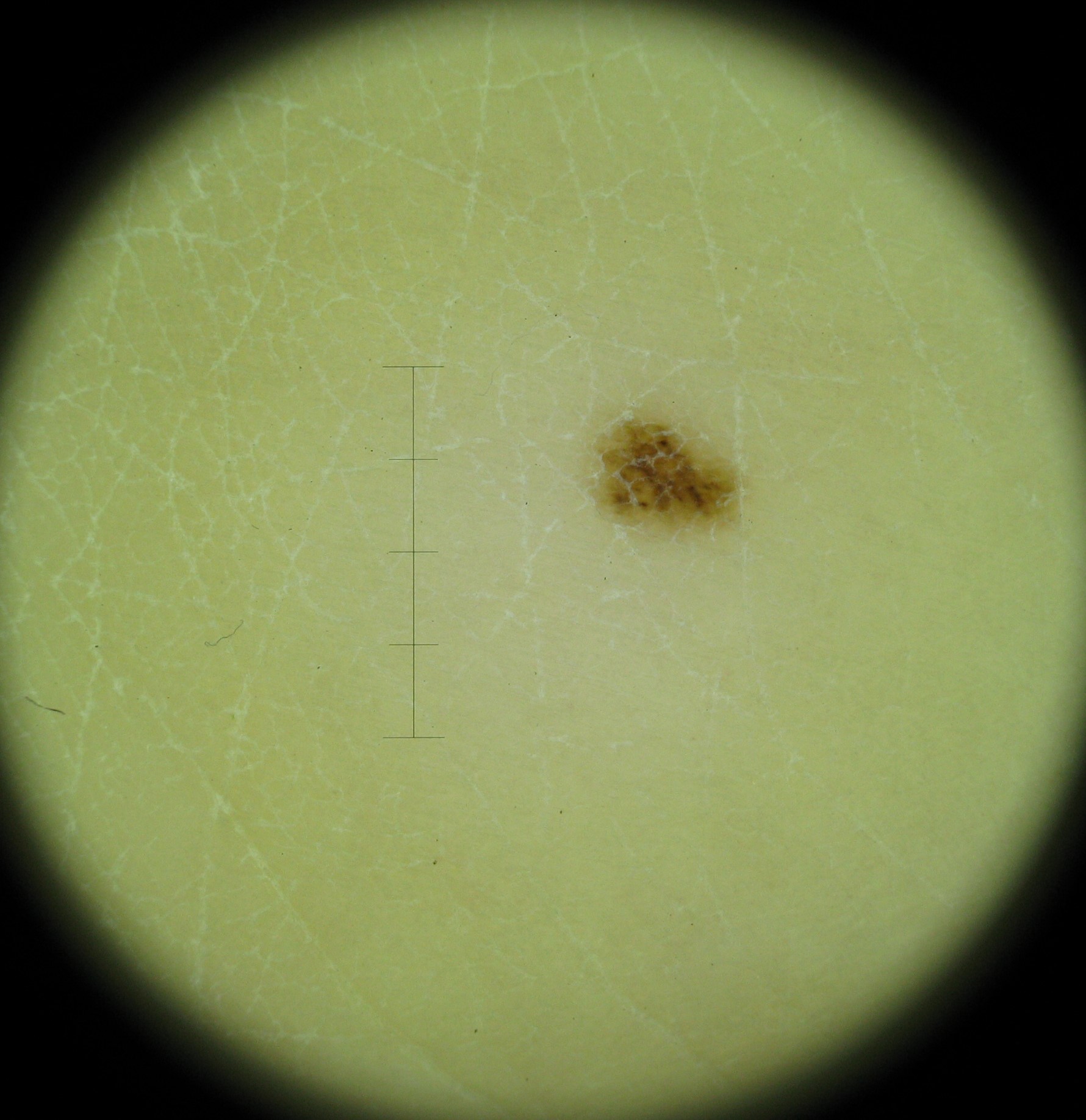Findings: A dermoscopic image of a skin lesion. Impression: Consistent with an acral dysplastic junctional nevus.